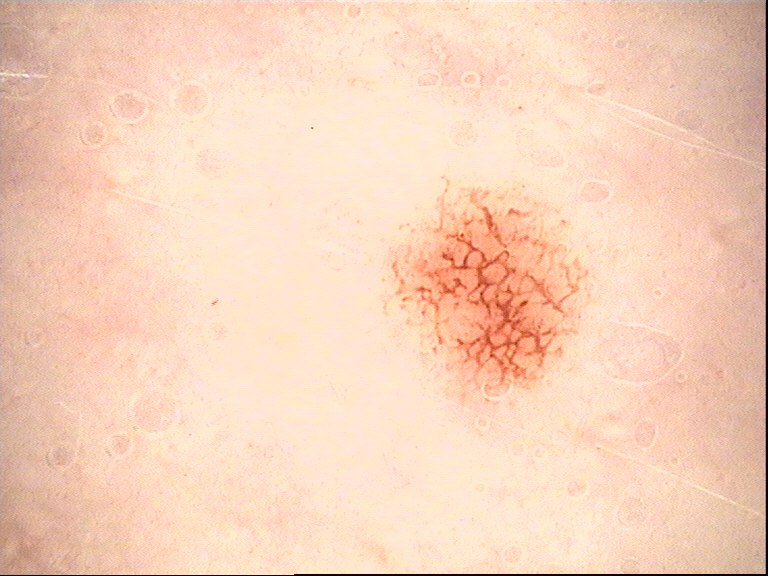A dermoscopic image of a skin lesion.
Classified as a benign lesion — a dysplastic junctional nevus.